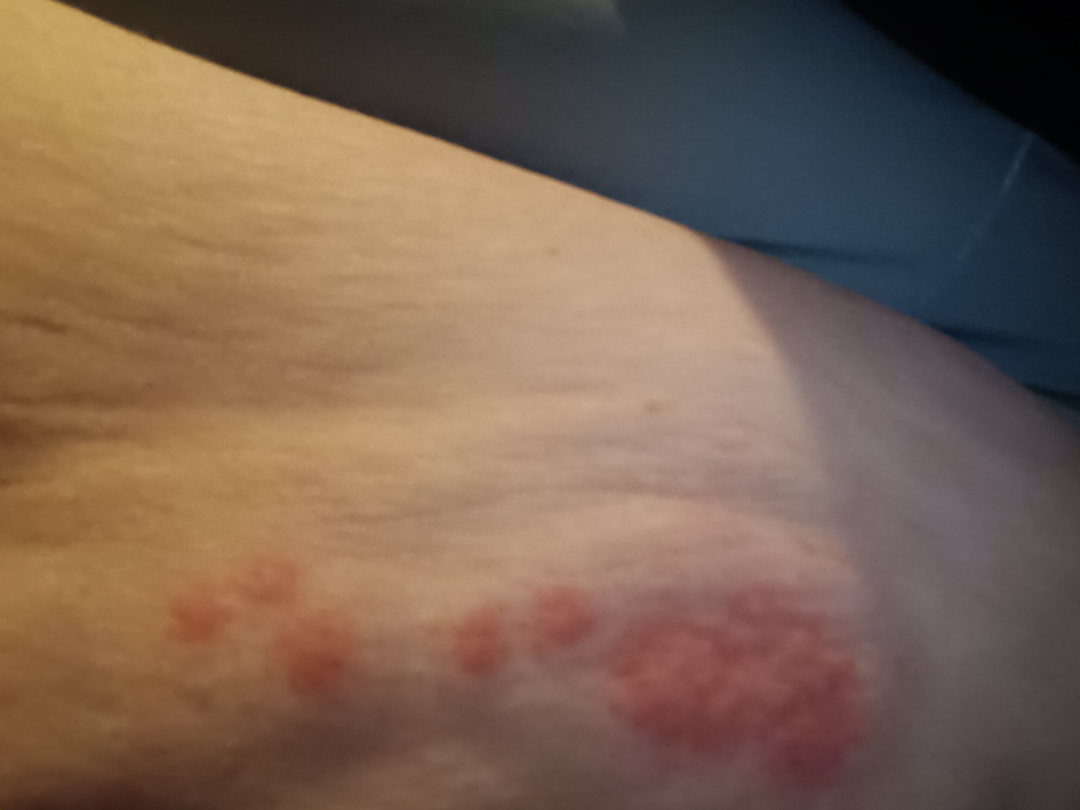Notes:
- assessment: unable to determine
- photo taken: close-up
- described texture: raised or bumpy
- patient-reported symptoms: itching and enlargement
- patient's own categorization: a rash
- duration: about one day
- body site: leg